The patient is a female aged 18–29. The leg, front of the torso and back of the torso are involved. The photograph is a close-up of the affected area: 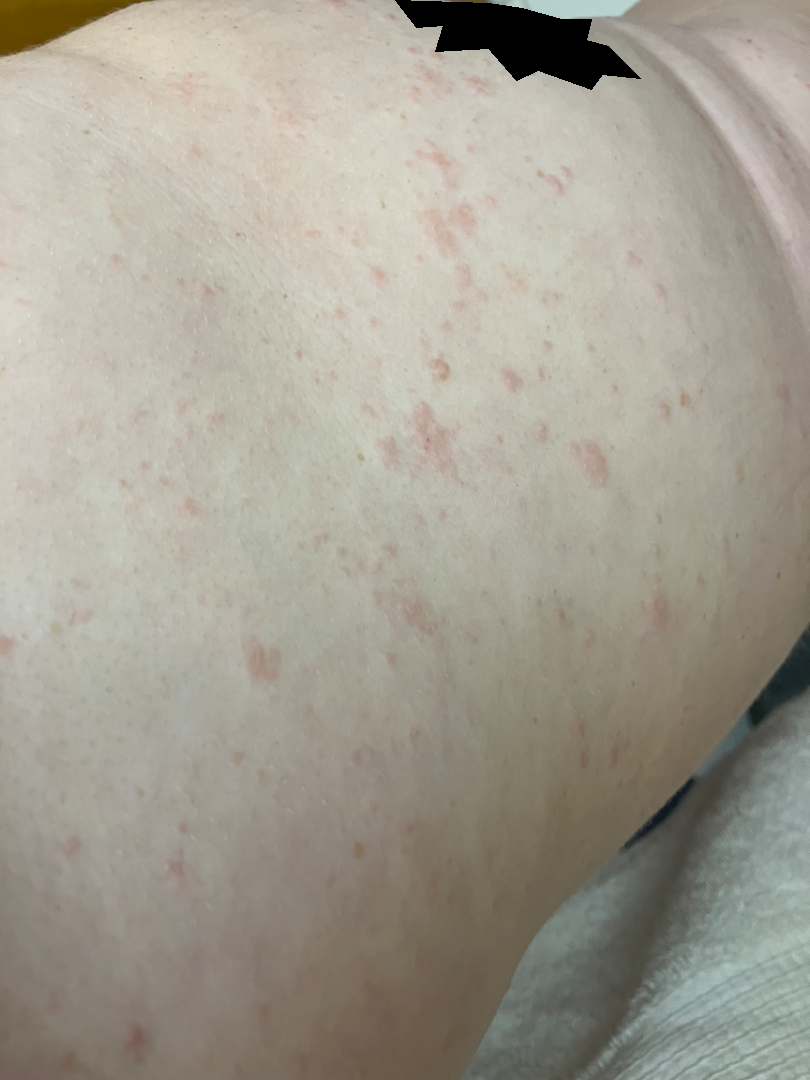Findings: In keeping with Urticaria.